A patient 45 years old; a clinical photo of a skin lesion taken with a smartphone — 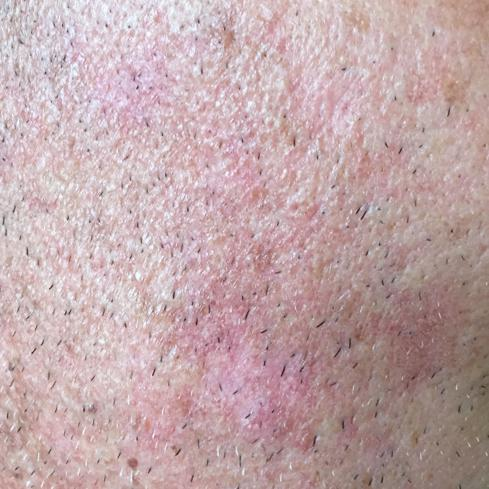Clinical context:
Located on the face. By the patient's account, the lesion itches, but is not elevated.
Conclusion:
Consistent with an actinic keratosis.